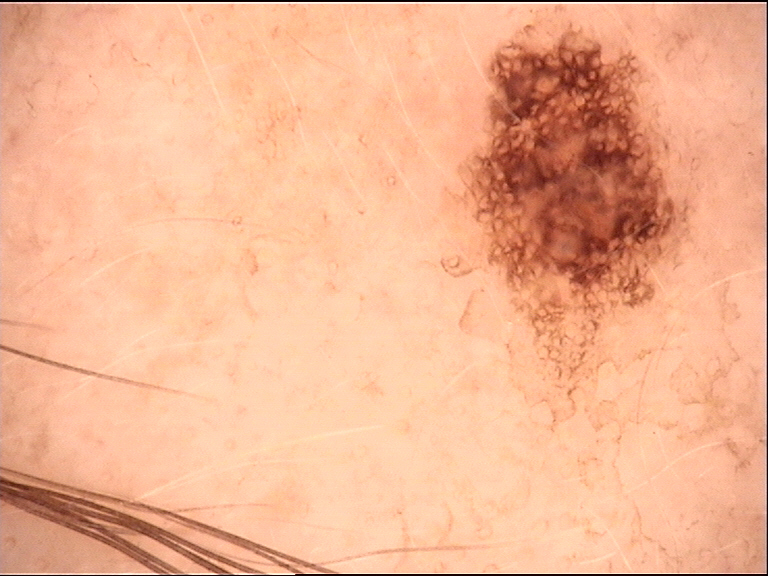Consistent with a dysplastic junctional nevus.